A macroscopic clinical photograph of a skin lesion. A moderate number of moles by the patient's own estimate. Collected as part of a research study, without a referral diagnosis. The patient says their skin reddens with sun exposure. A female patient 20 years old — 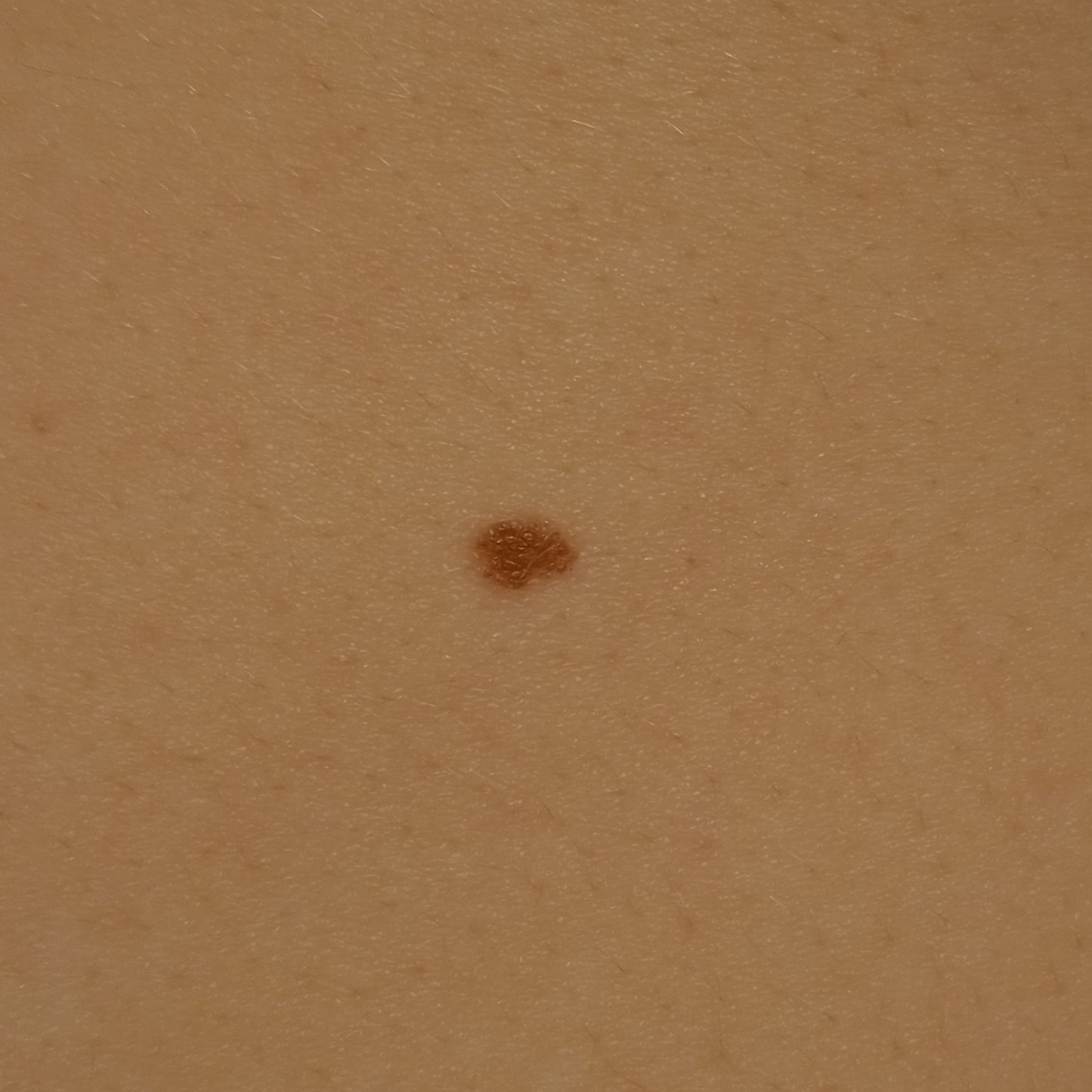Findings:
* site — the torso
* diagnosis — melanocytic nevus (dermatologist consensus)